The lesion involves the front of the torso · this is a close-up image: 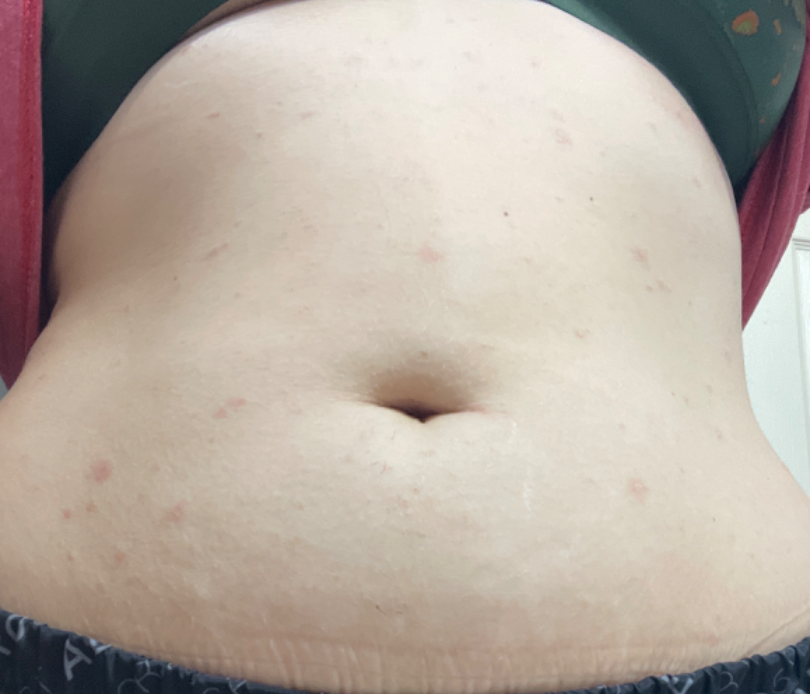| feature | finding |
|---|---|
| other reported symptoms | fatigue, shortness of breath, chills and joint pain |
| skin tone | Fitzpatrick II |
| patient describes the issue as | a rash |
| texture | rough or flaky |
| symptoms | itching, enlargement, bothersome appearance and burning |
| symptom duration | one to four weeks |
| diagnostic considerations | favoring Pityriasis rosea; also raised was Psoriasis; less likely is Pityriasis lichenoides |